The patient indicates itching and burning · the patient indicates the condition has been present for less than one week · located on the leg · self-categorized by the patient as a rash · the patient indicates the lesion is flat · the patient reported no systemic symptoms · the photo was captured at a distance.
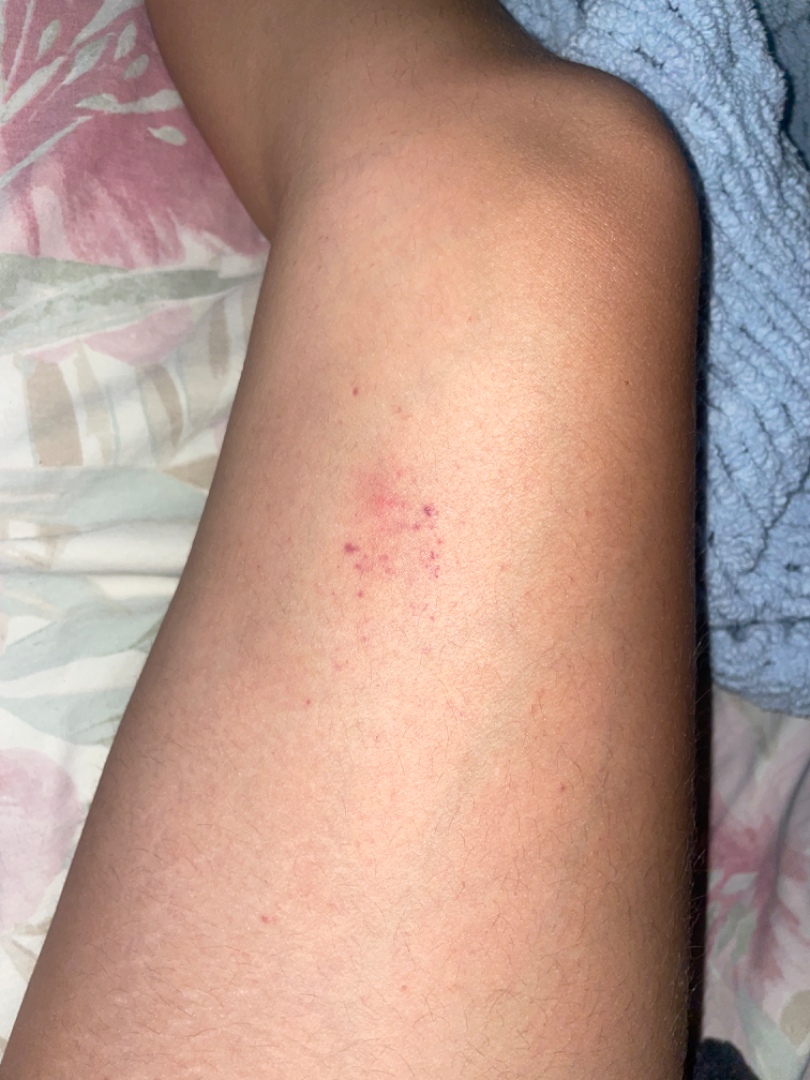Assessment: The dermatologist could not determine a likely condition from the photograph alone.